The photo was captured at a distance · the subject is female:
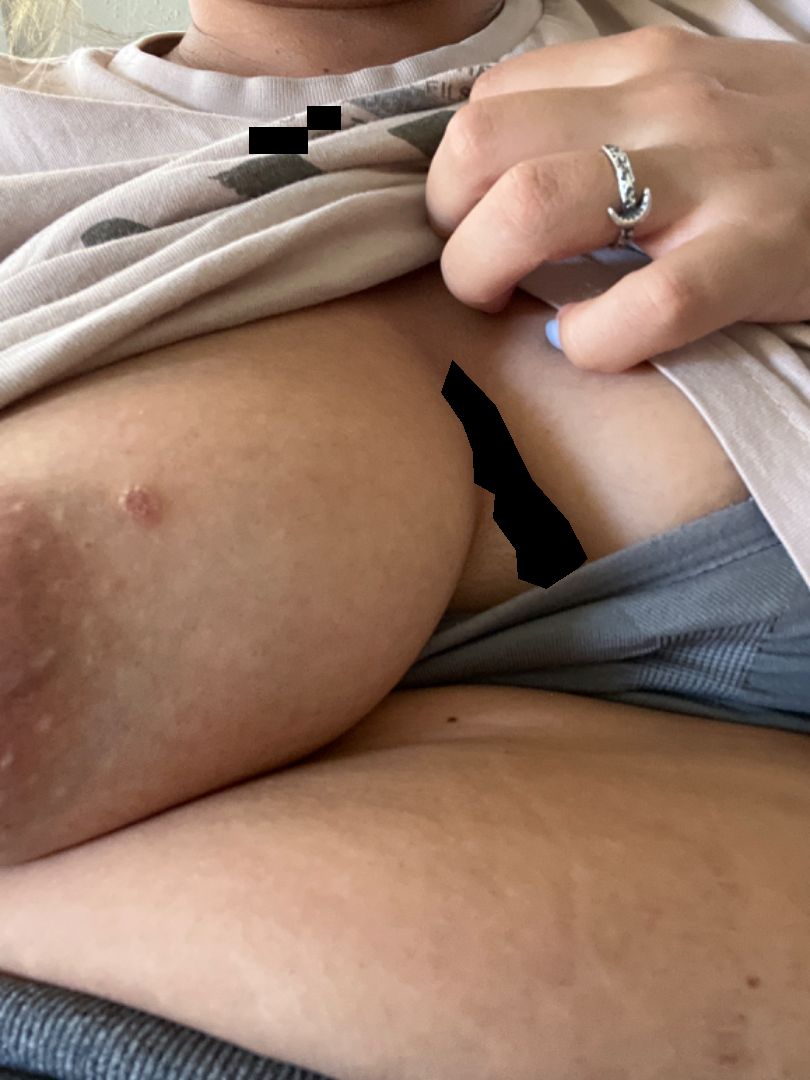patient describes the issue as — a rash
patient-reported symptoms — itching
duration — one to three months
associated systemic symptoms — none reported
surface texture — fluid-filled, rough or flaky and raised or bumpy
differential diagnosis — Eczema, Abscess and Impetigo were considered with similar weight